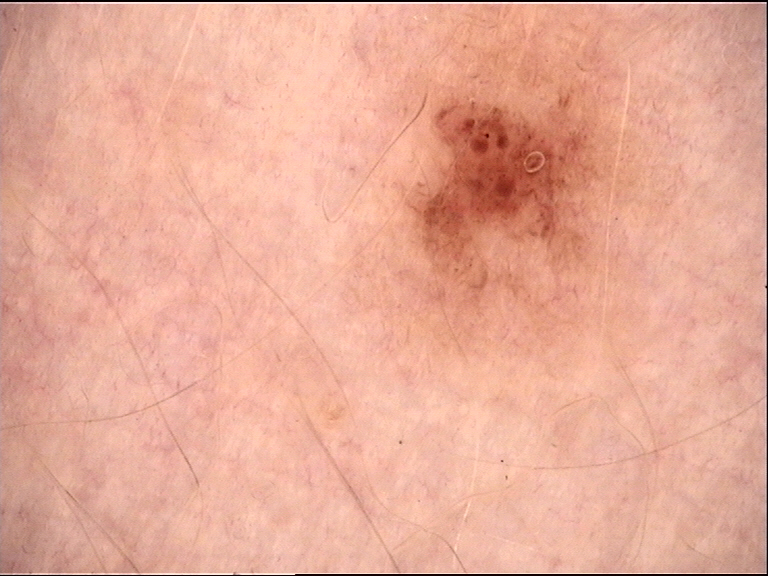Classified as a junctional nevus.